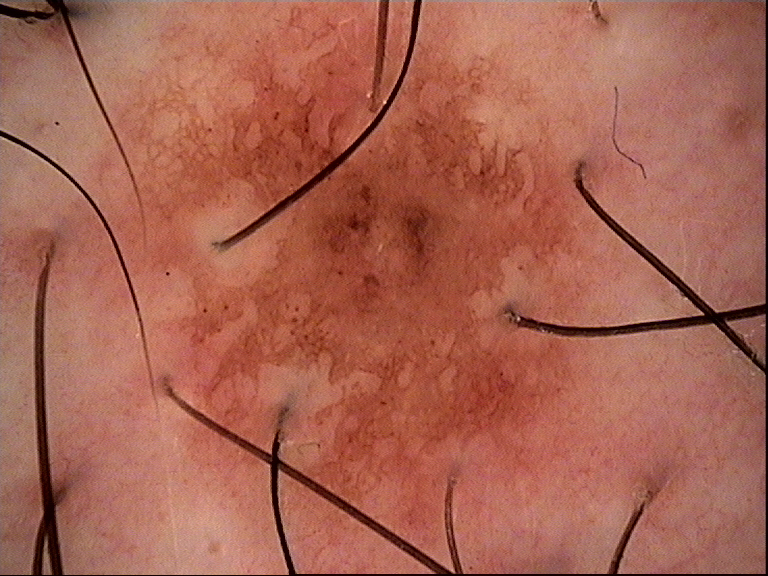modality = dermatoscopy | classification = banal | assessment = compound nevus (expert consensus).